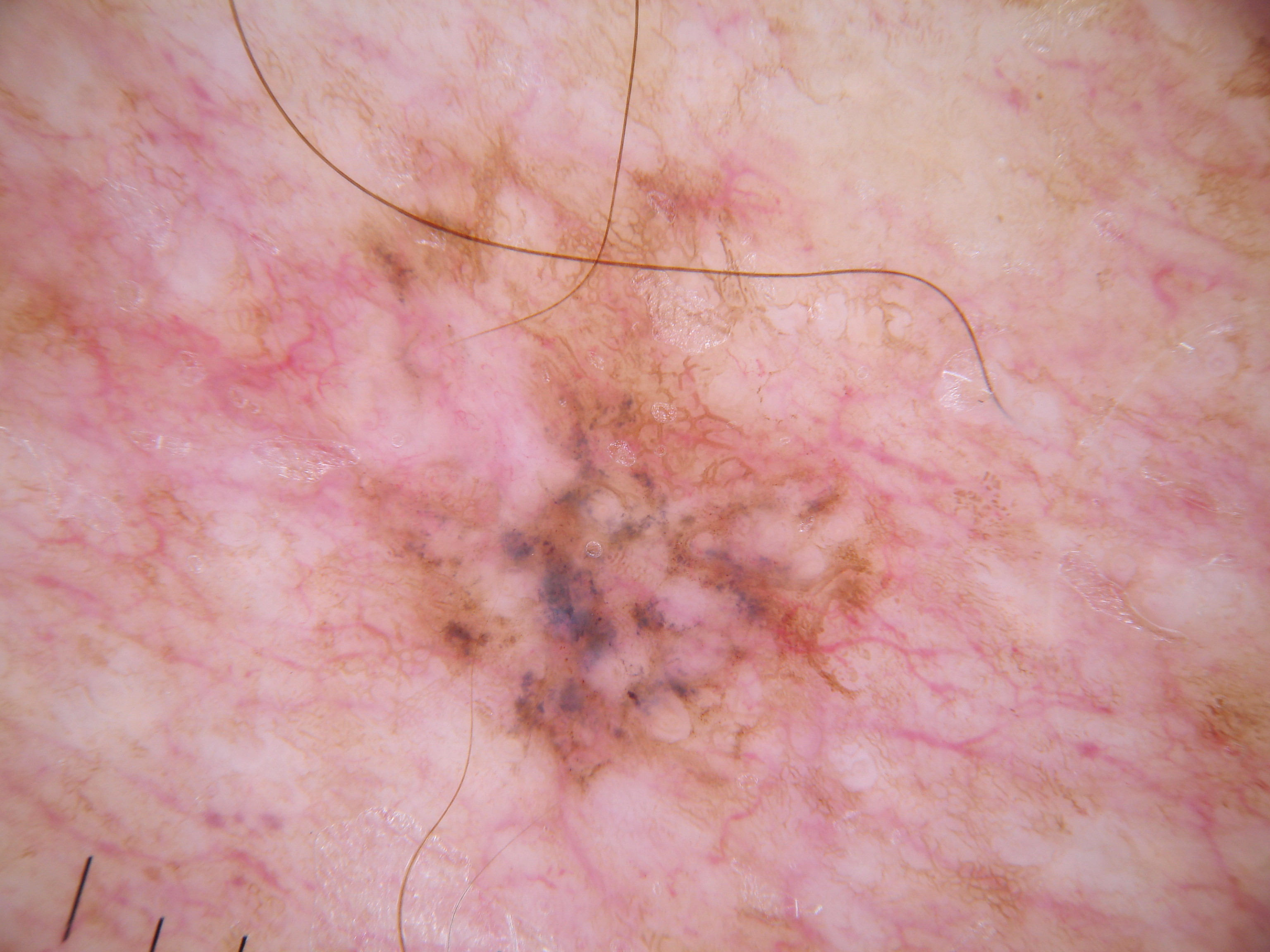image type — dermoscopy; bounding box — 336 371 919 809; assessment — a melanoma, a malignant skin lesion.